A dermoscopic image of a skin lesion:
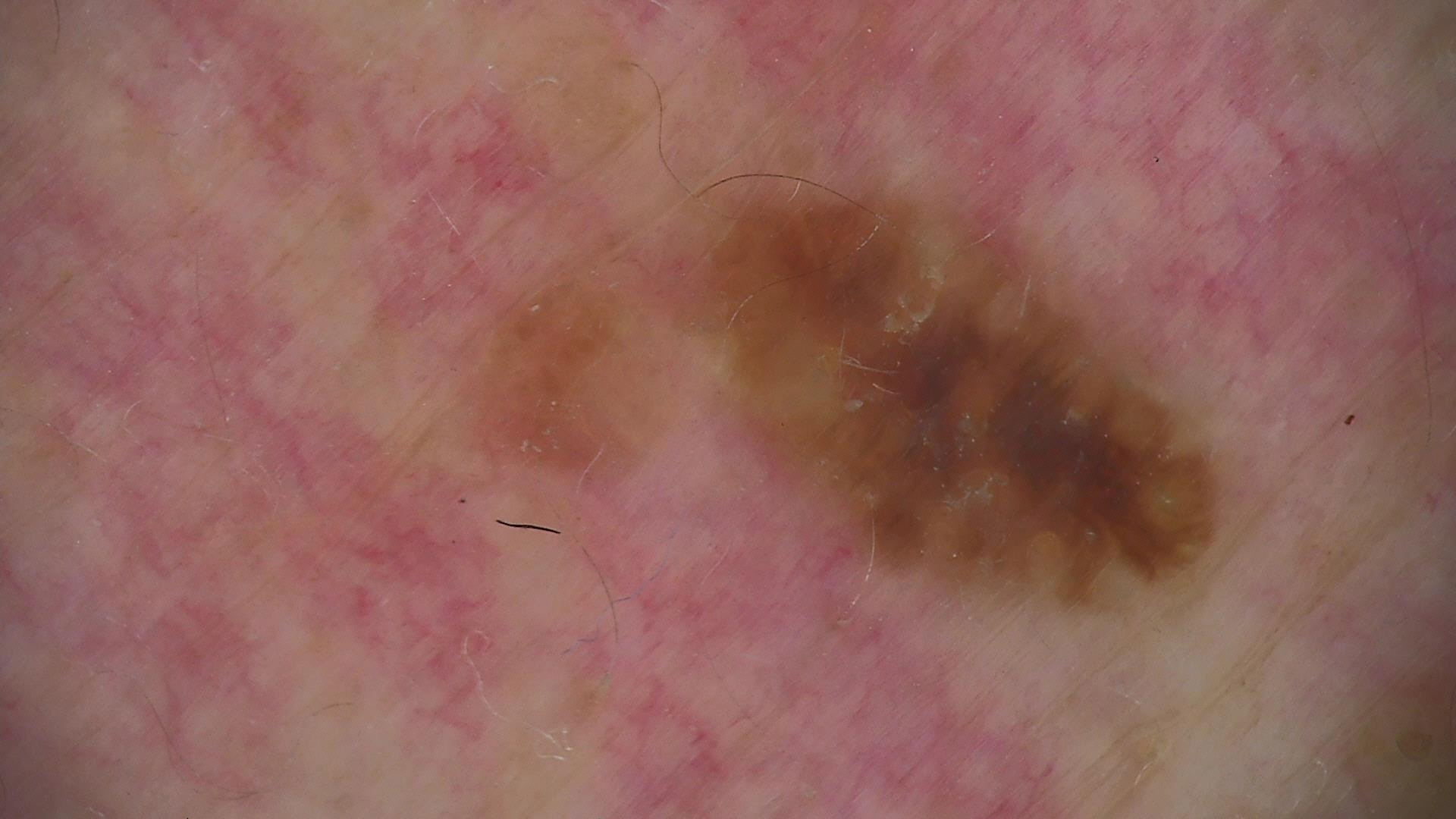Case:
The architecture is that of a keratinocytic lesion.
Impression:
The diagnostic label was a seborrheic keratosis.